A dermoscopic photograph of a skin lesion.
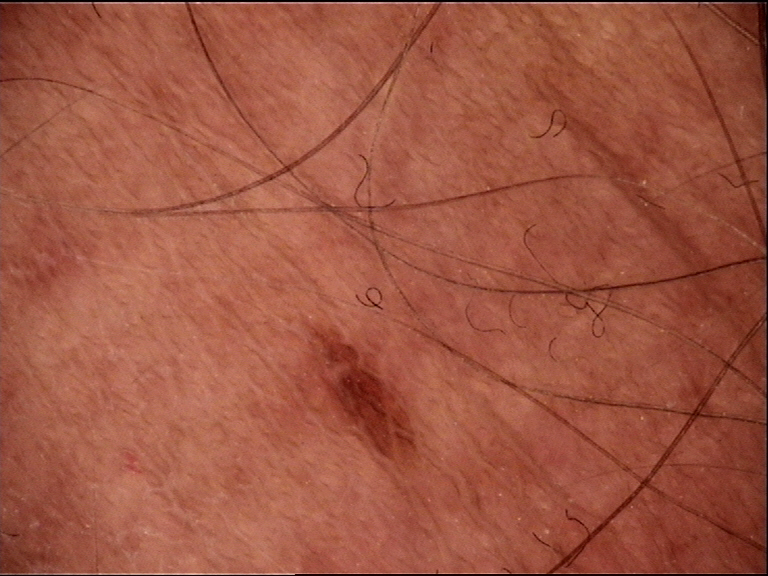label — junctional nevus (expert consensus).